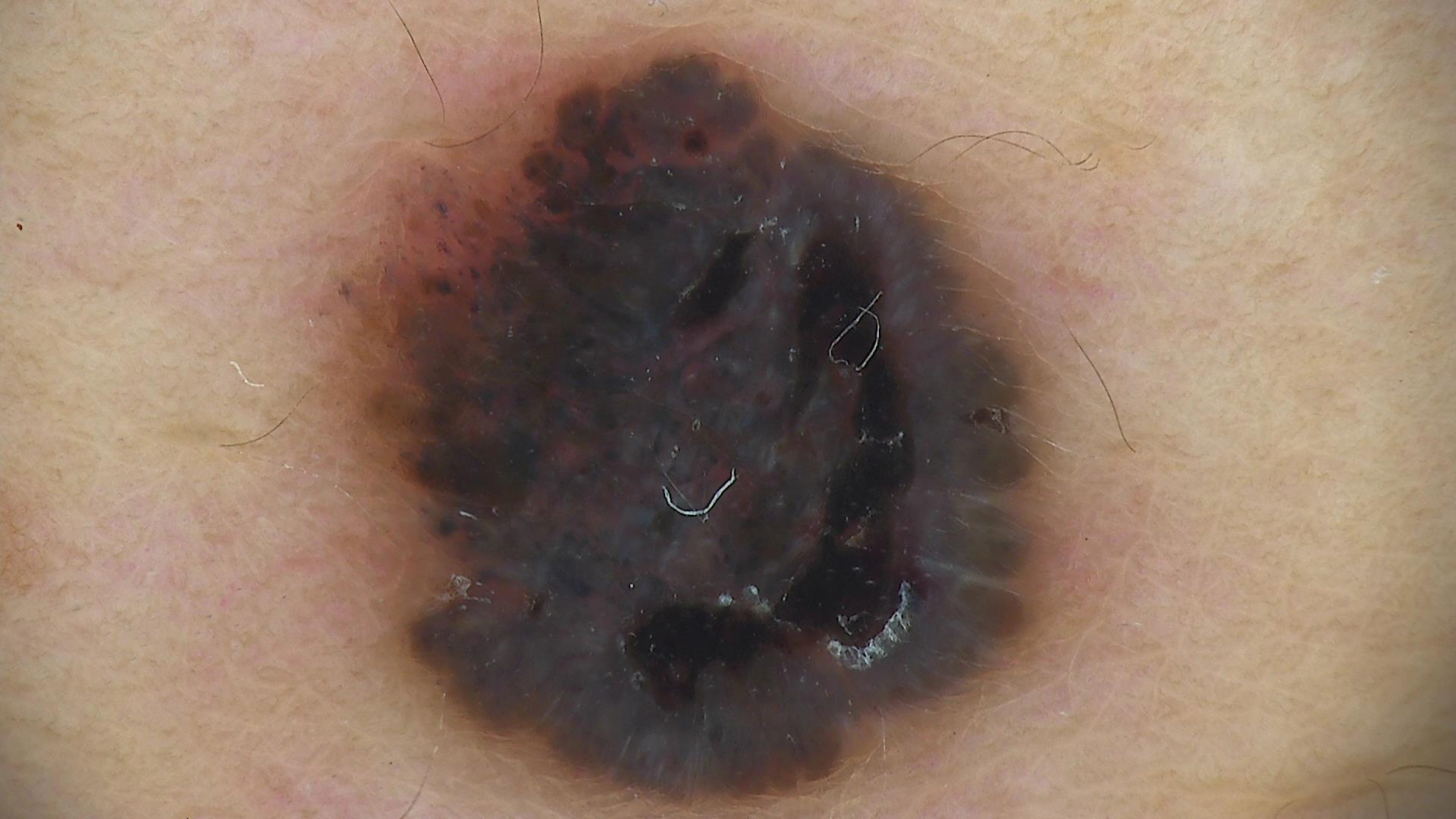The biopsy diagnosis was a melanoma.